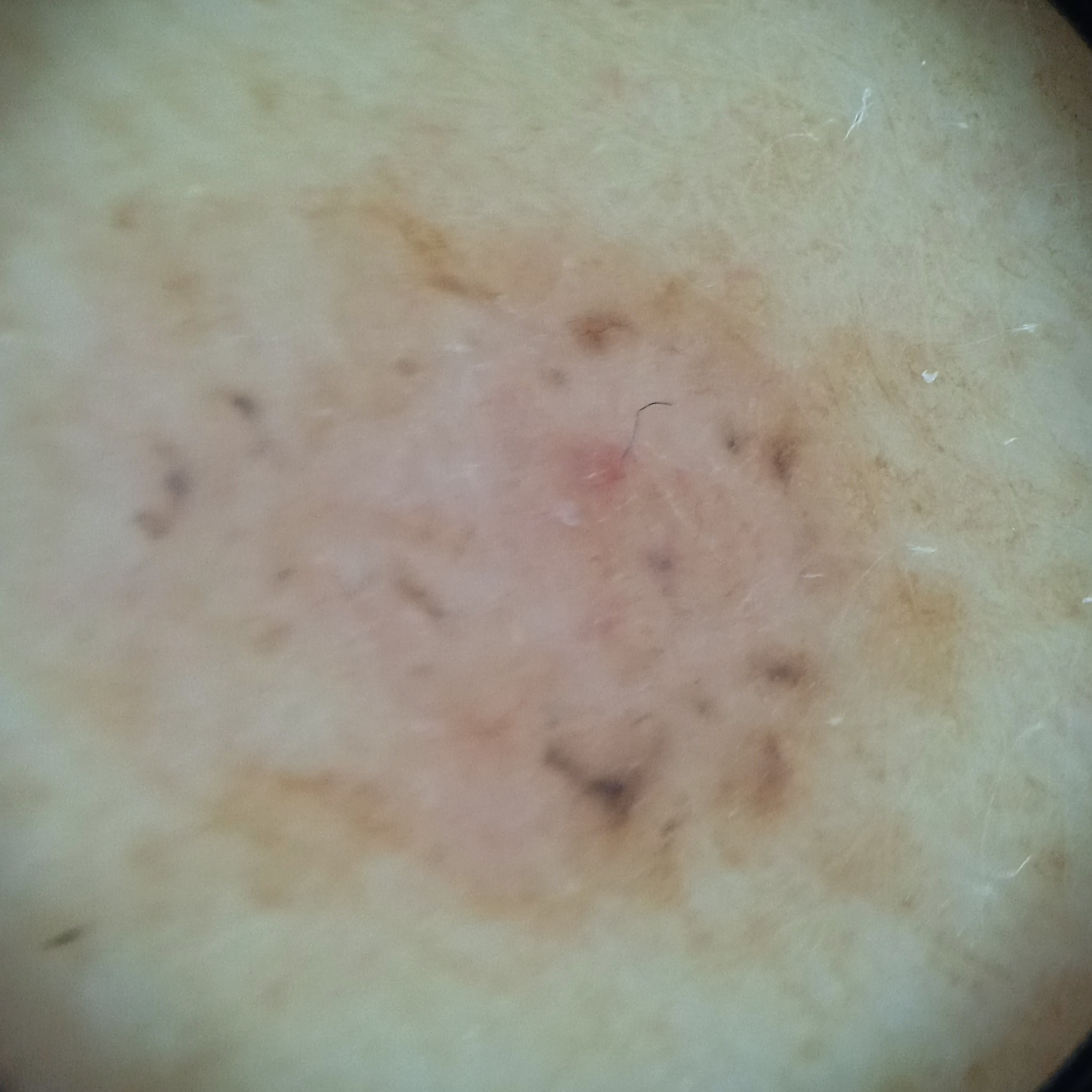Referred with a clinical suspicion of basal cell carcinoma.
A female patient 64 years of age.
A dermoscopic image of a skin lesion.
Confirmed on histopathology as a basal cell carcinoma, following excision, with a measured tumor thickness of 1 mm.